A dermoscopic close-up of a skin lesion:
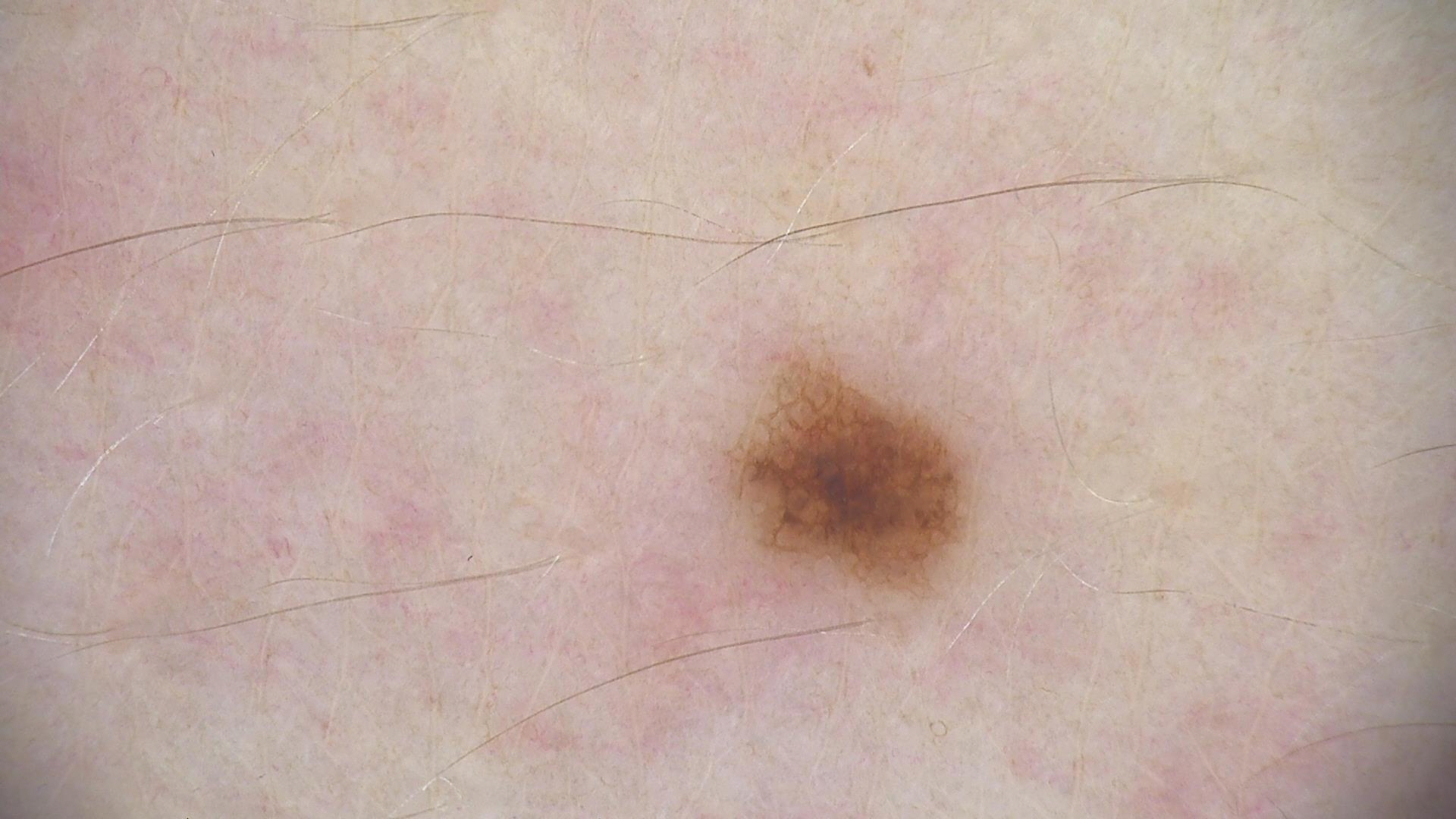Diagnosed as a benign lesion — a dysplastic junctional nevus.